A dermoscopic image of a skin lesion:
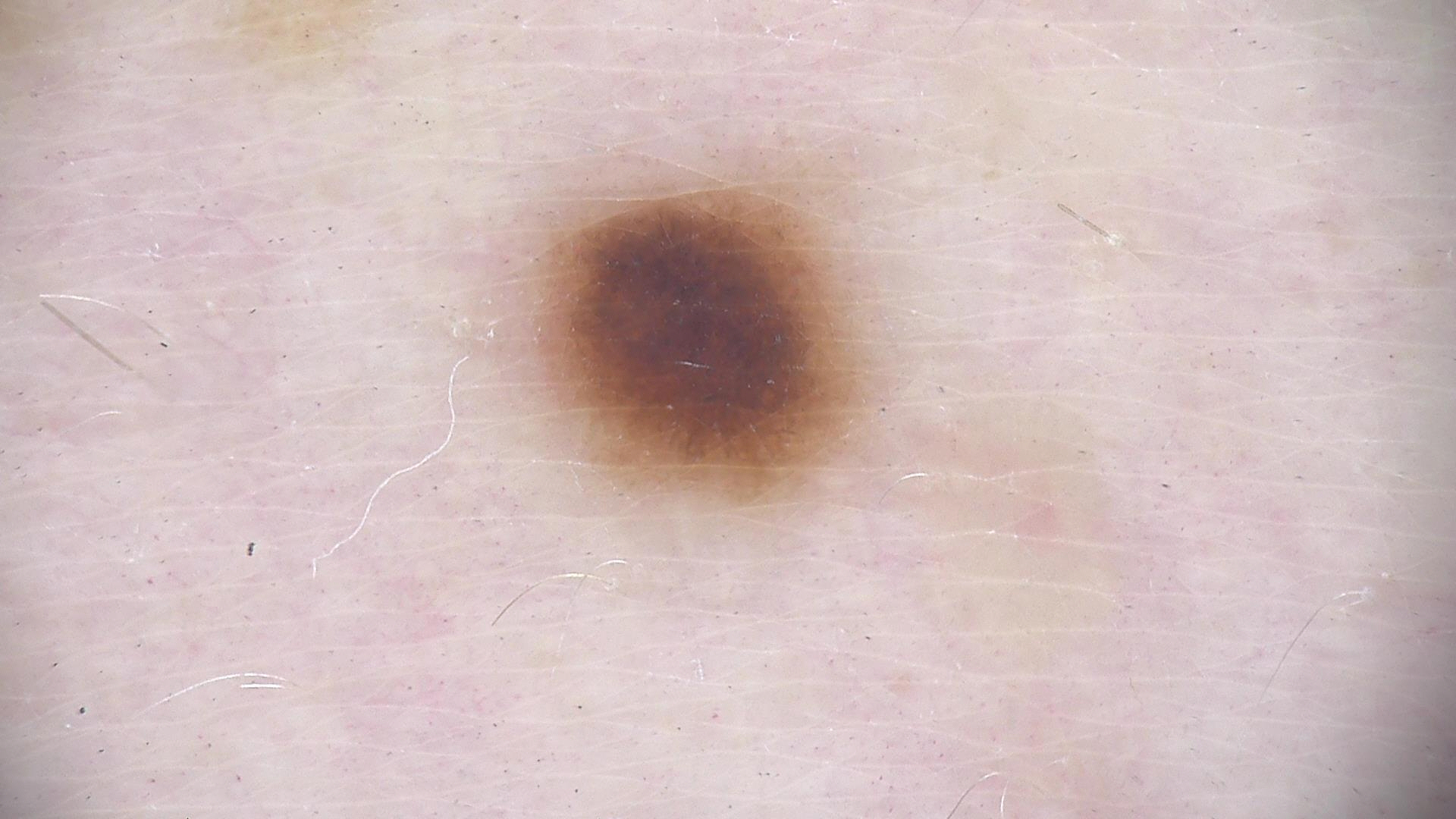Impression: Consistent with a benign lesion — a dysplastic junctional nevus.